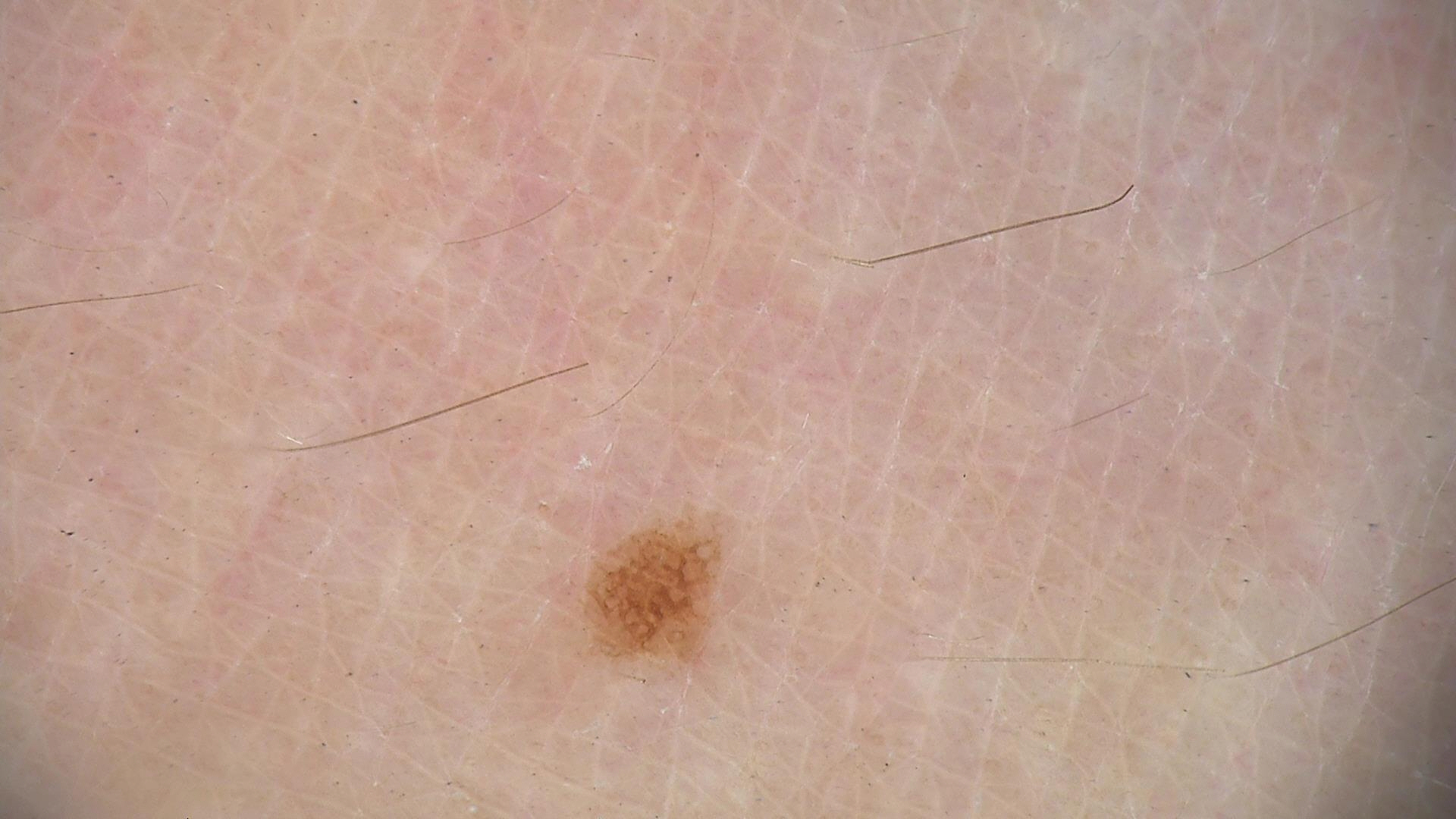Dermoscopy of a skin lesion.
Classified as a dysplastic junctional nevus.